The photograph was taken at a distance, located on the leg — 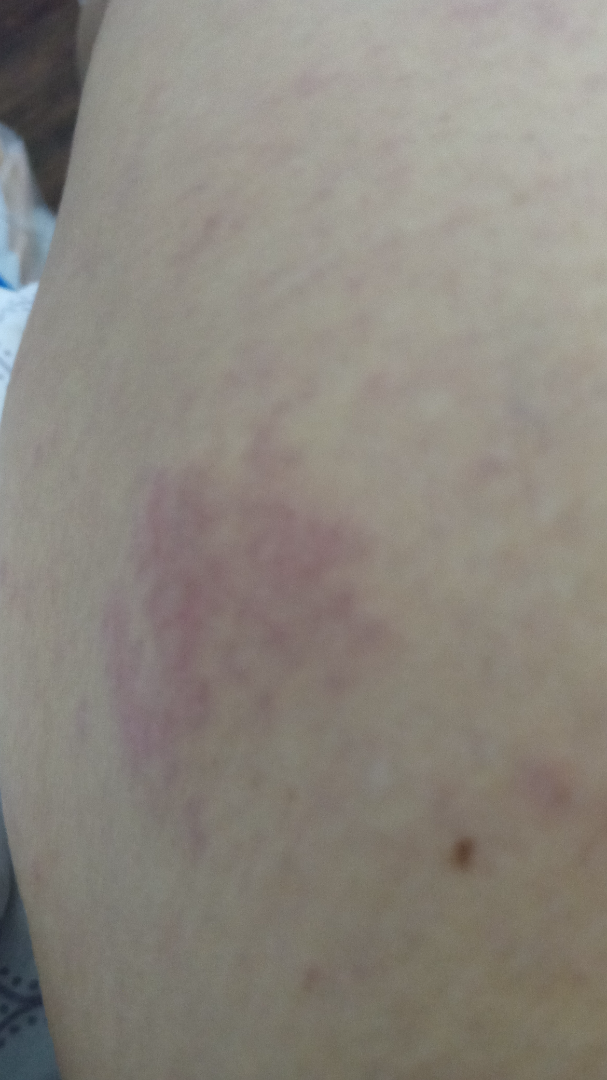Findings:
The skin findings could not be characterized from the image.
Background:
Self-categorized by the patient as a rash. The patient reports bothersome appearance and itching. The lesion is described as raised or bumpy.